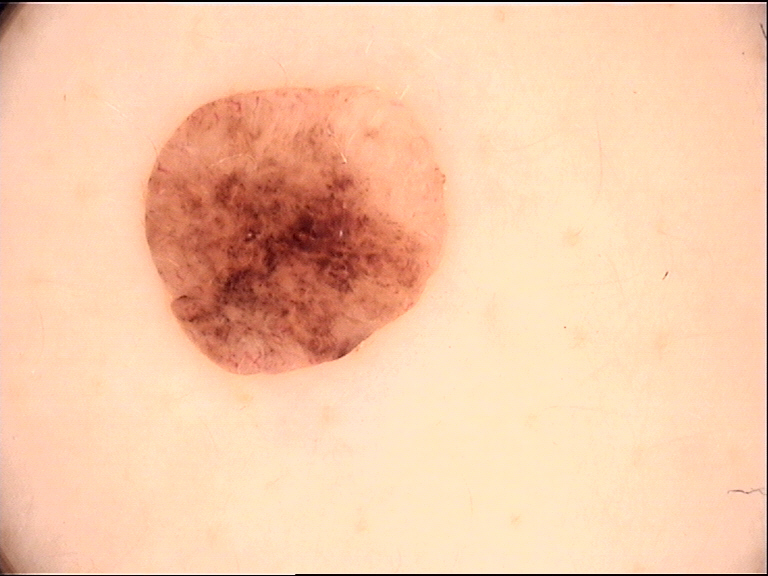diagnostic label = dermal nevus (expert consensus).